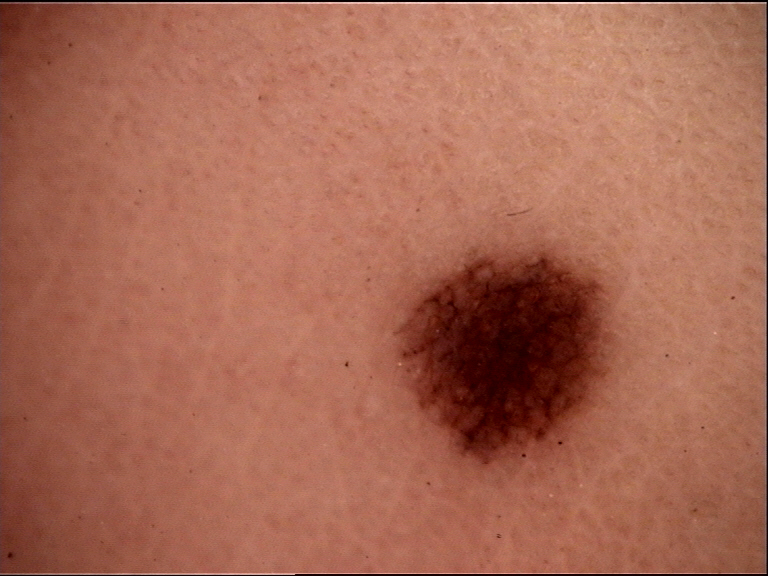{"image": "dermoscopy", "diagnosis": {"name": "junctional nevus", "code": "jb", "malignancy": "benign", "super_class": "melanocytic", "confirmation": "expert consensus"}}